The patient describes having few moles overall; a female patient aged 60; referred with a clinical suspicion of basal cell carcinoma; on a questionnaire the patient reported a personal history of cancer and a personal history of skin cancer; a dermatoscopic image of a skin lesion; the patient says their skin tans without first burning:
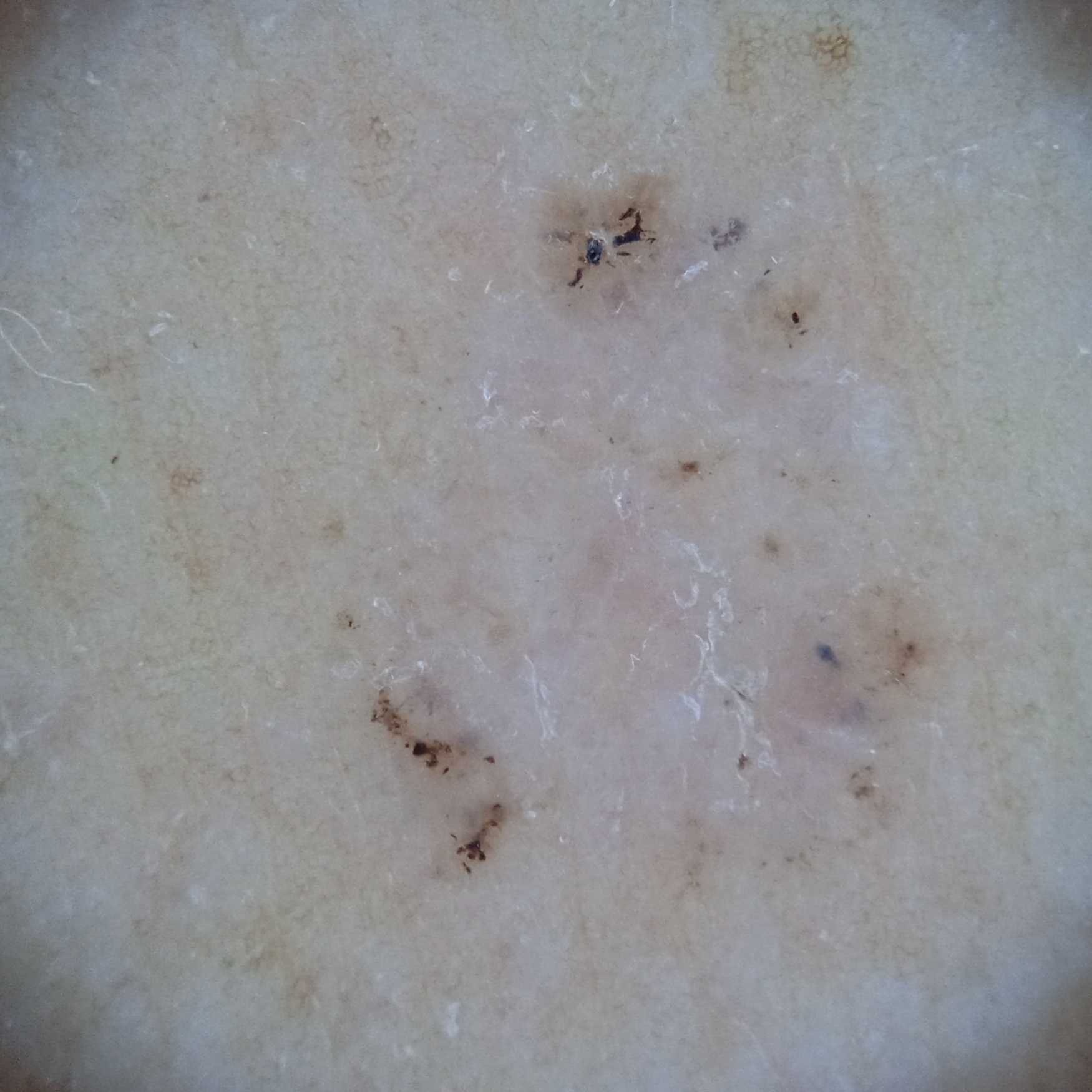The diagnostic impression was a basal cell carcinoma.